A clinical close-up photograph of a skin lesion. Recorded as Fitzpatrick II. A female patient 66 years of age: 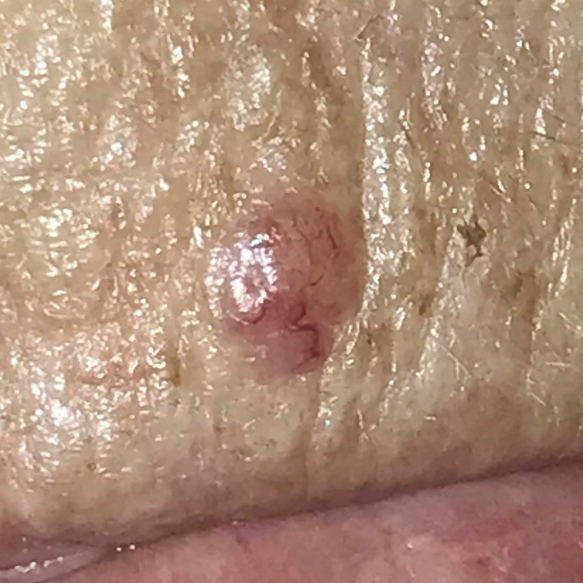| feature | finding |
|---|---|
| site | the face |
| diameter | 3 × 2 mm |
| reported symptoms | itching, elevation / no bleeding, no pain |
| diagnosis | basal cell carcinoma (biopsy-proven) |